The photo was captured at a distance; the affected area is the arm: 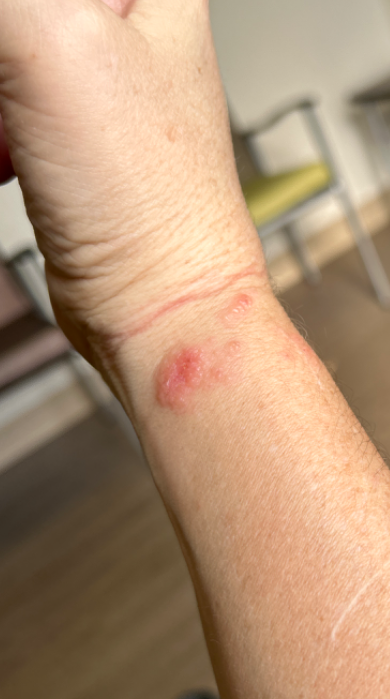assessment — ungradable on photographic review.